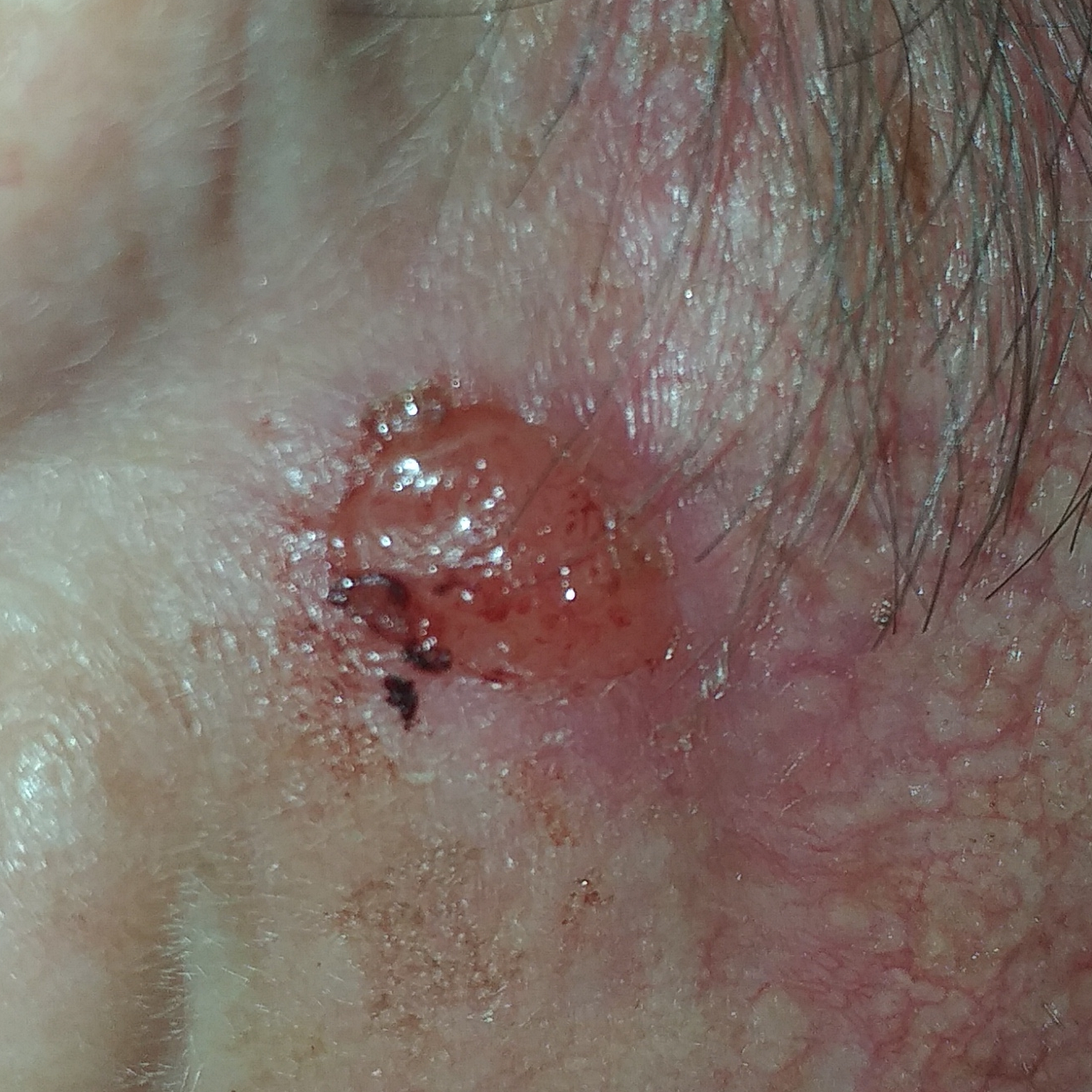Histopathologically confirmed as a basal cell carcinoma.